A dermoscopic photograph of a skin lesion.
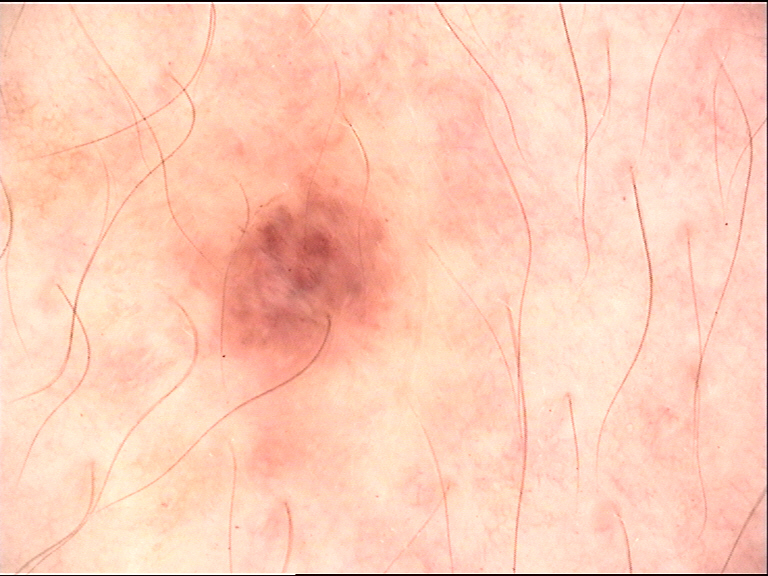Q: What is the diagnosis?
A: dysplastic compound nevus (expert consensus)